A male subject age 83 · collected as part of a research study, without a referral diagnosis · a clinical photograph showing a skin lesion.
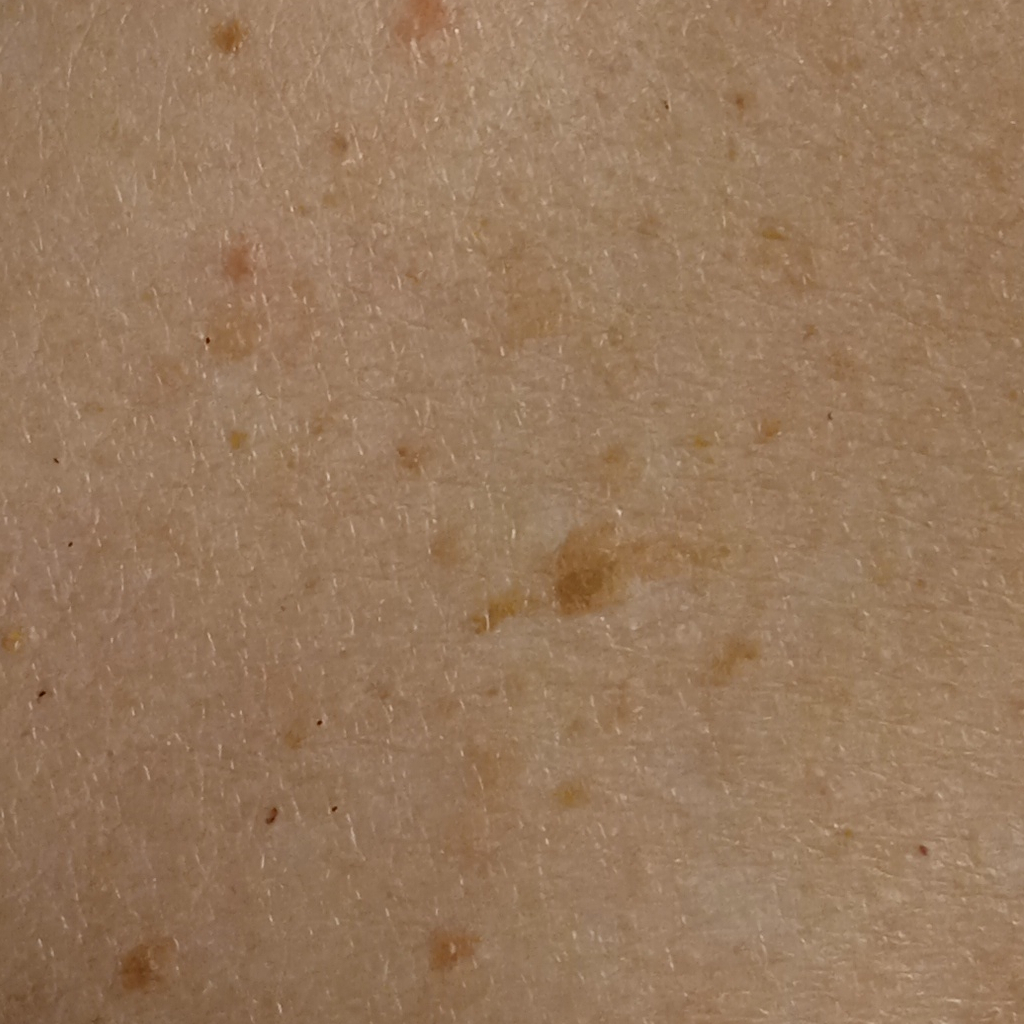Case:
- body site: the back
- lesion size: 16.4 mm
- diagnosis: seborrheic keratosis (dermatologist consensus)